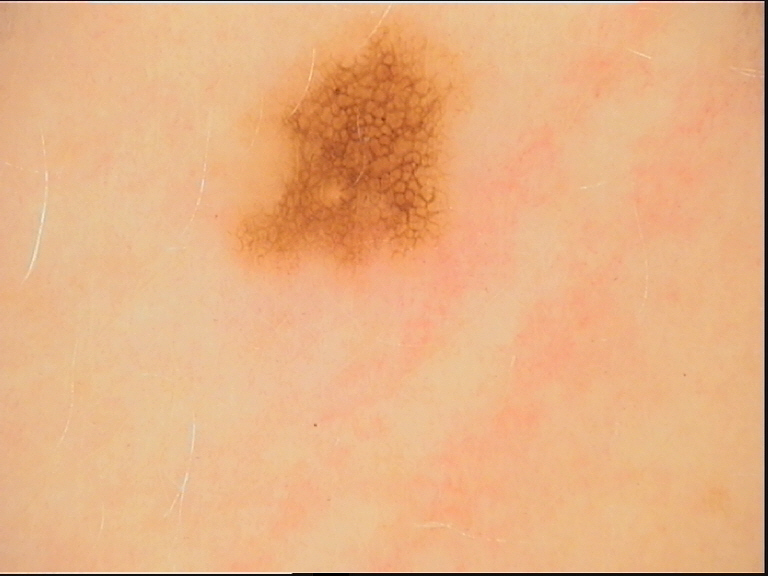Case:
* image type — dermatoscopy
* class — dysplastic junctional nevus (expert consensus)